Dermoscopy of a skin lesion: 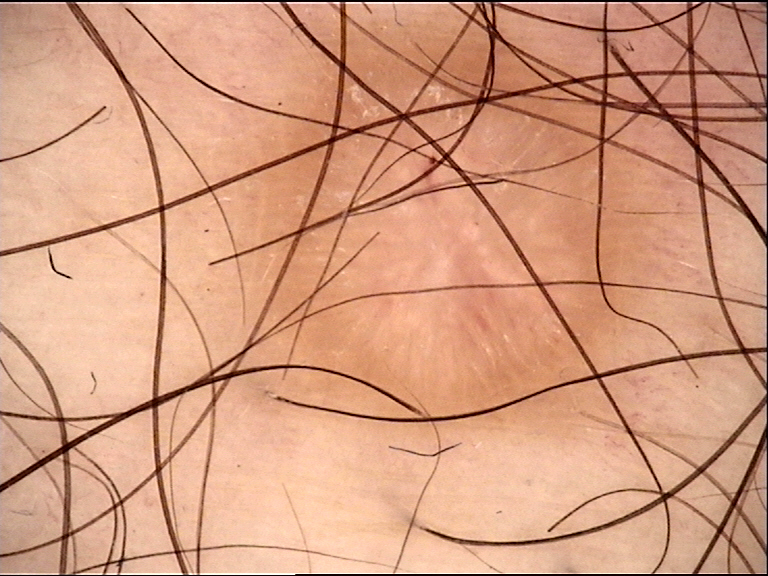The architecture is that of a fibro-histiocytic lesion. Labeled as a benign lesion — a dermatofibroma.